A dermatoscopic image of a skin lesion: 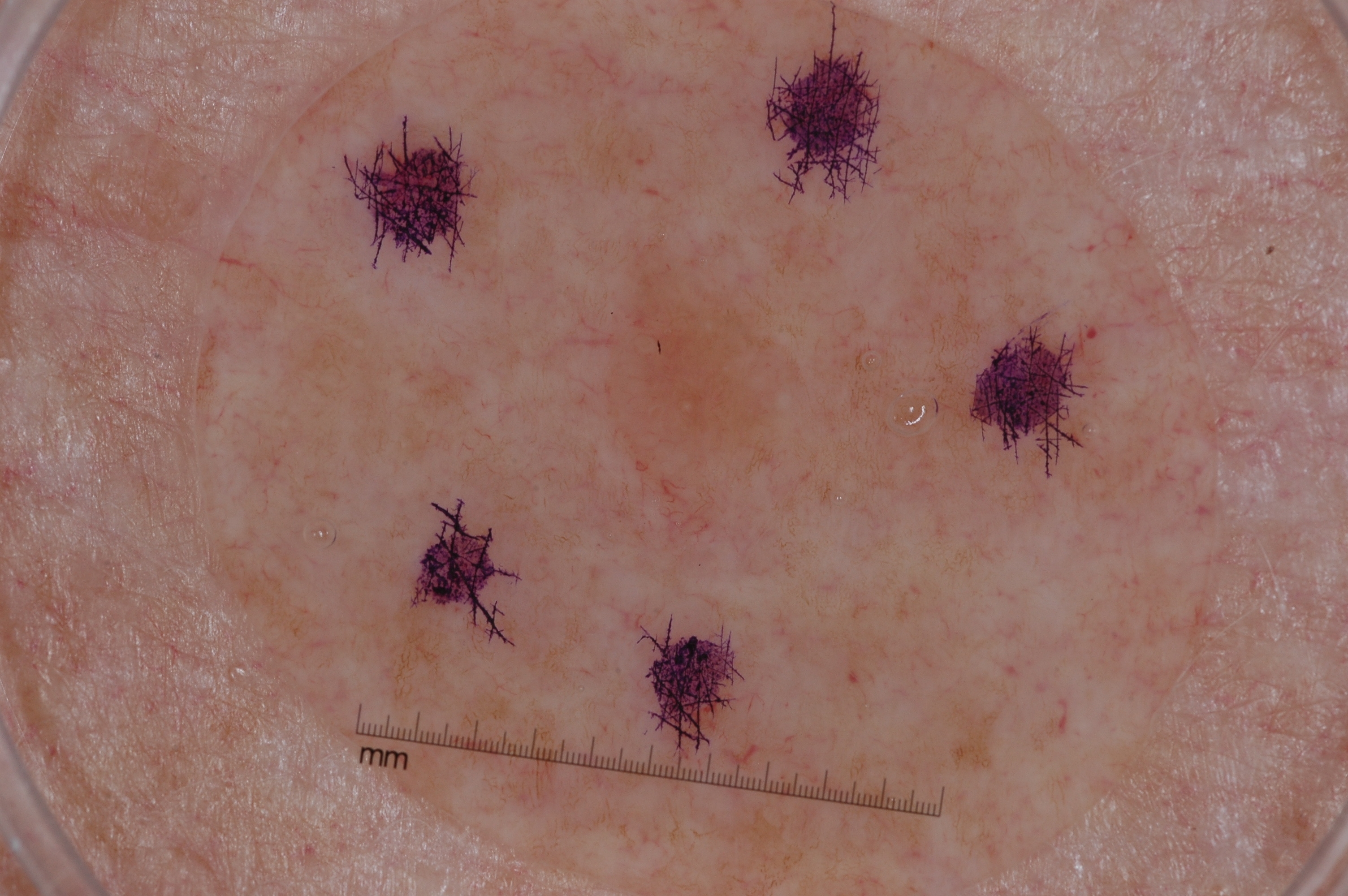The lesion is located at left=594, top=243, right=843, bottom=532.
Dermoscopic review identifies milia-like cysts.
The lesion was assessed as a melanocytic nevus.